A male subject approximately 20 years of age · contact-polarized dermoscopy of a skin lesion.
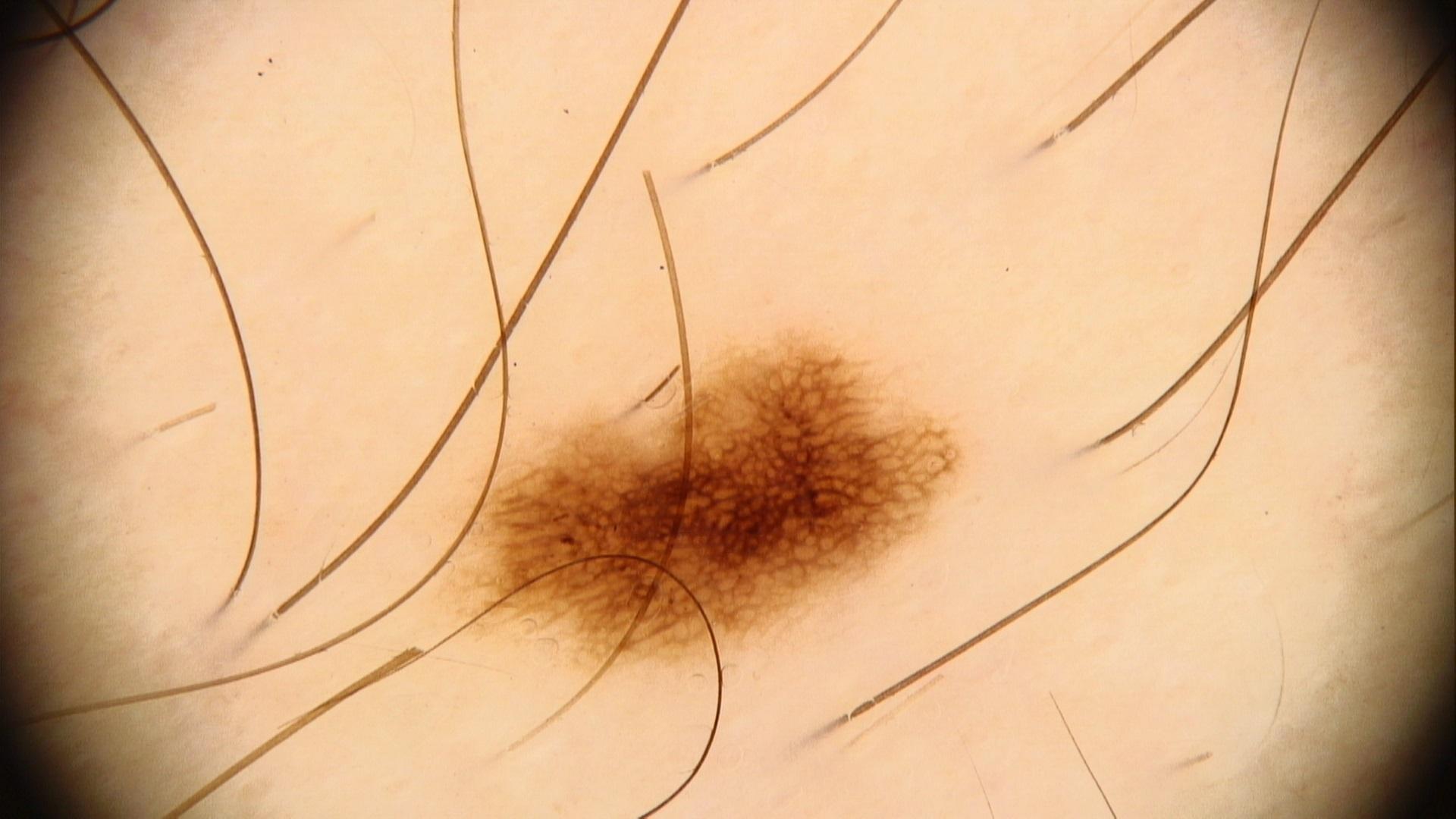location: a lower extremity; impression: Nevus.